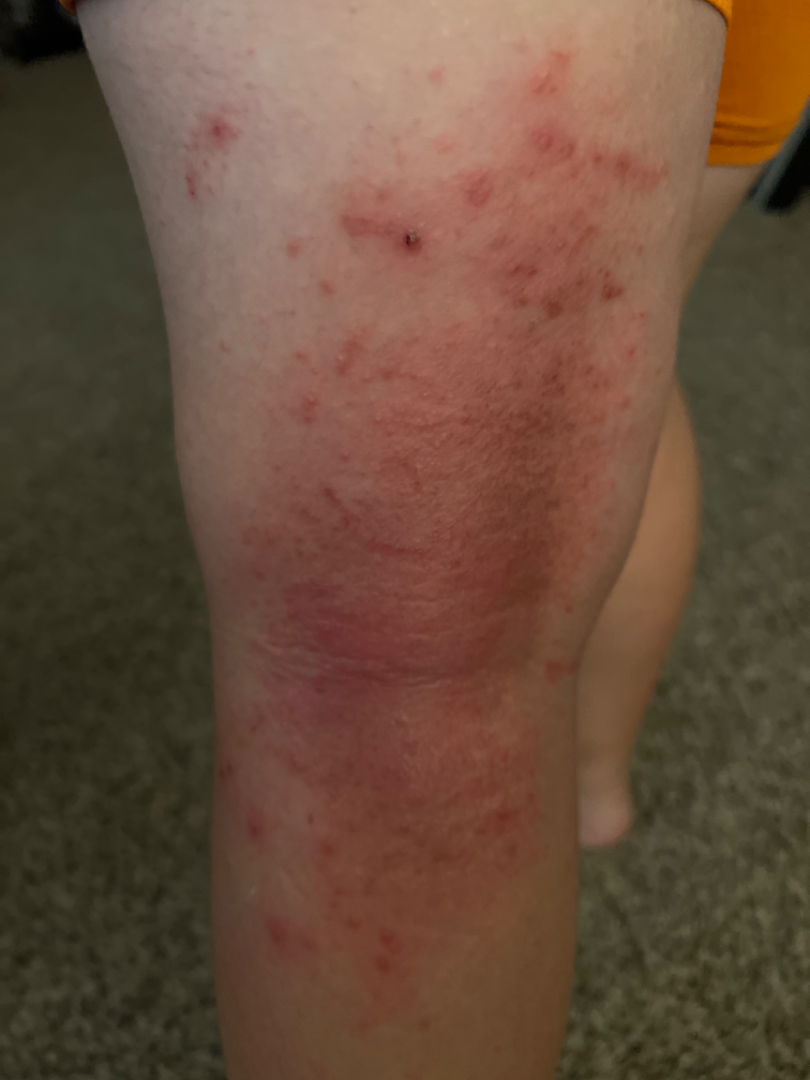Background:
The patient notes darkening, itching, bothersome appearance and enlargement. Texture is reported as rough or flaky and raised or bumpy. Fitzpatrick phototype II; human graders estimated 2 on the MST. The photograph is a close-up of the affected area. Self-categorized by the patient as skin that appeared healthy to them. The affected area is the leg.
Findings:
On remote review of the image, most consistent with Eczema; also consider Allergic Contact Dermatitis.